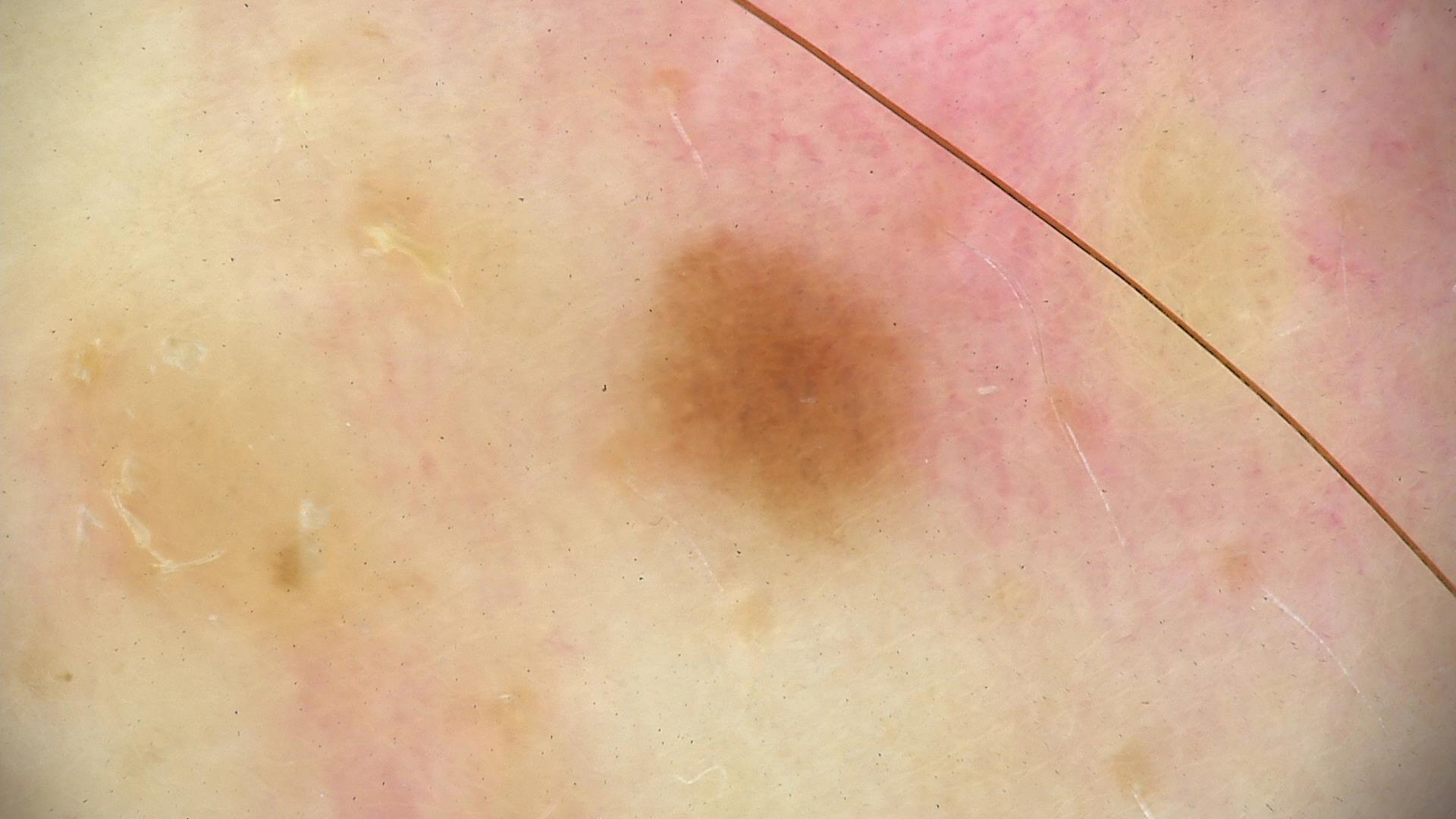Consistent with a dysplastic junctional nevus.